Texture is reported as raised or bumpy, rough or flaky and fluid-filled. The photo was captured at an angle. The lesion is associated with pain, bothersome appearance, enlargement, itching and burning. The affected area is the arm. Self-categorized by the patient as a rash. The patient notes associated fatigue. The patient is a female aged 30–39. Reported duration is one to four weeks.
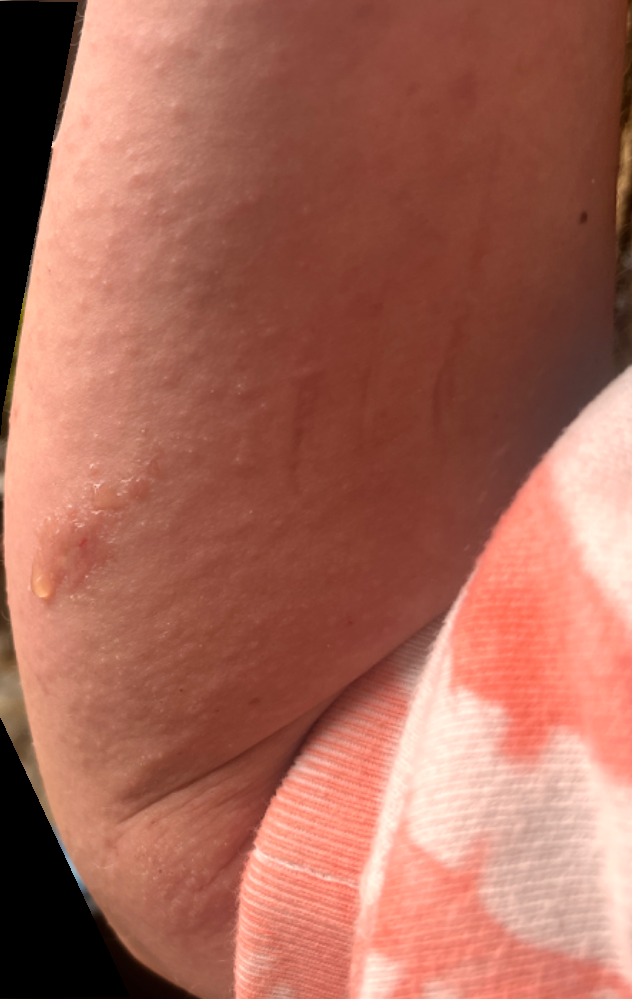Findings:
• assessment · not assessable